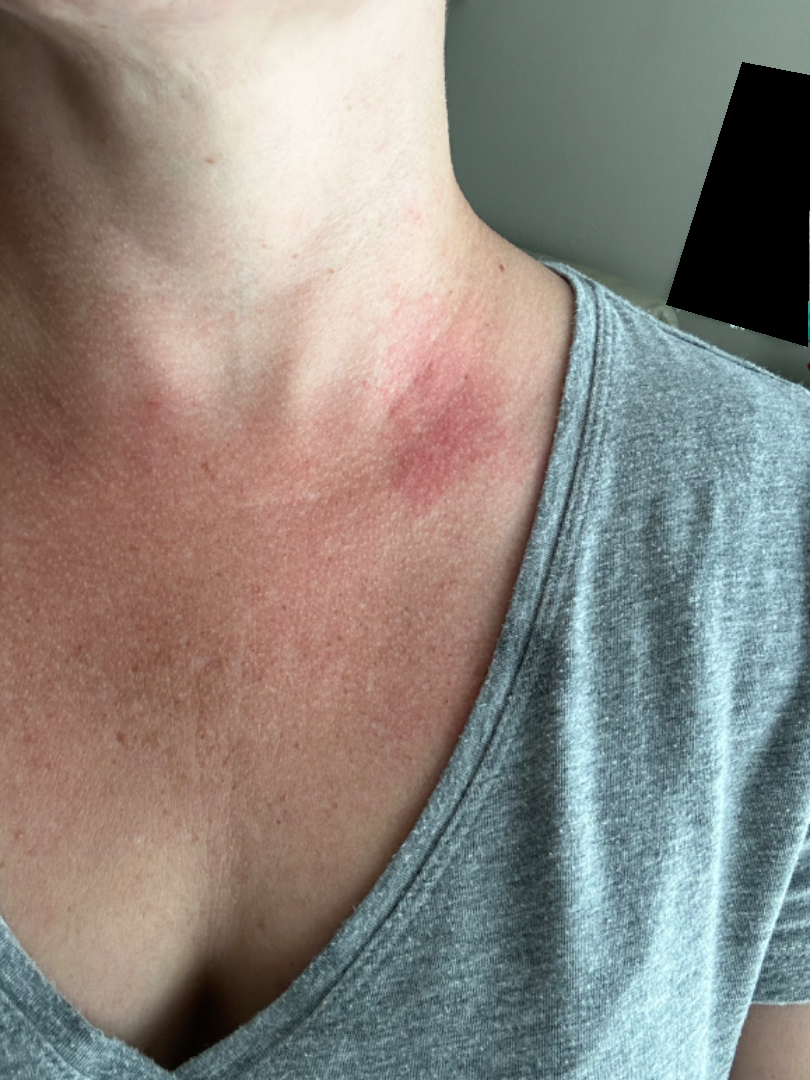– reported symptoms: none reported
– framing: at an angle
– texture: raised or bumpy and flat
– patient: female, age 30–39
– assessment: Berloque dermatitis, Allergic Contact Dermatitis and Irritant Contact Dermatitis were each considered, in no particular order